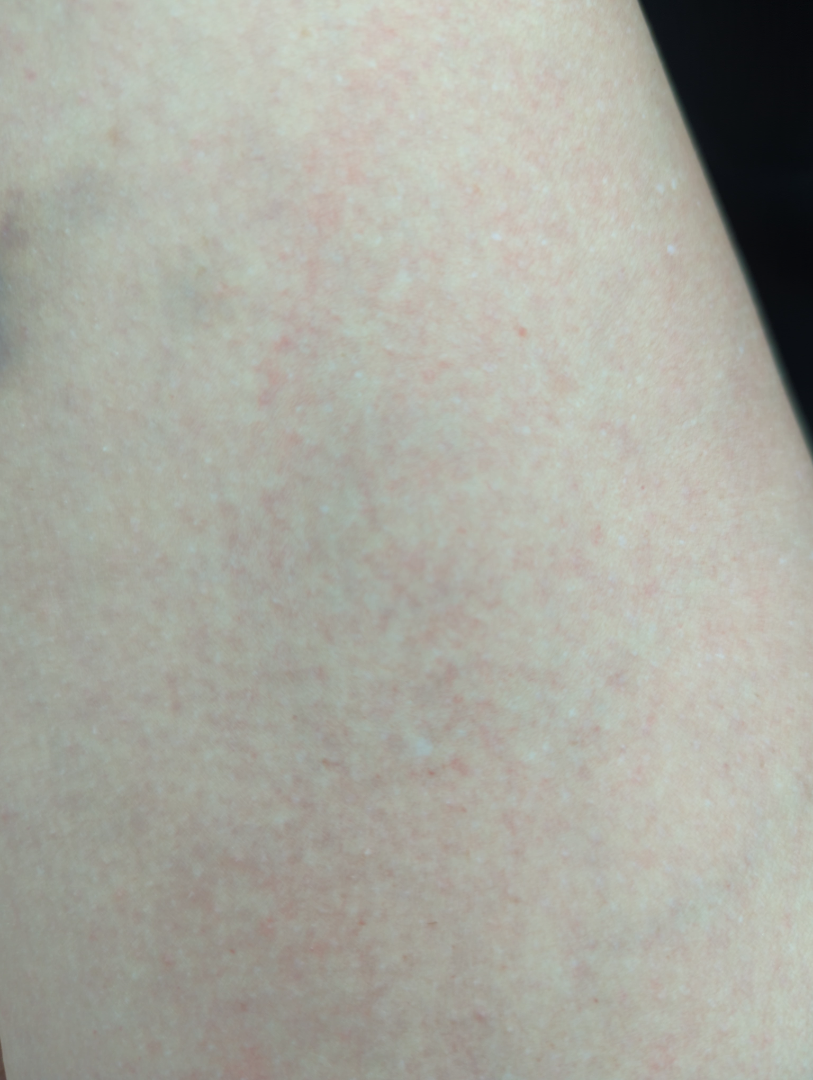  assessment: indeterminate
  body_site: leg
  shot_type: close-up